A clinical photograph showing a skin lesion. By history, prior skin cancer (patient or family), prior malignancy (patient or family), and no alcohol use. A female patient 75 years old. The patient is Fitzpatrick II — 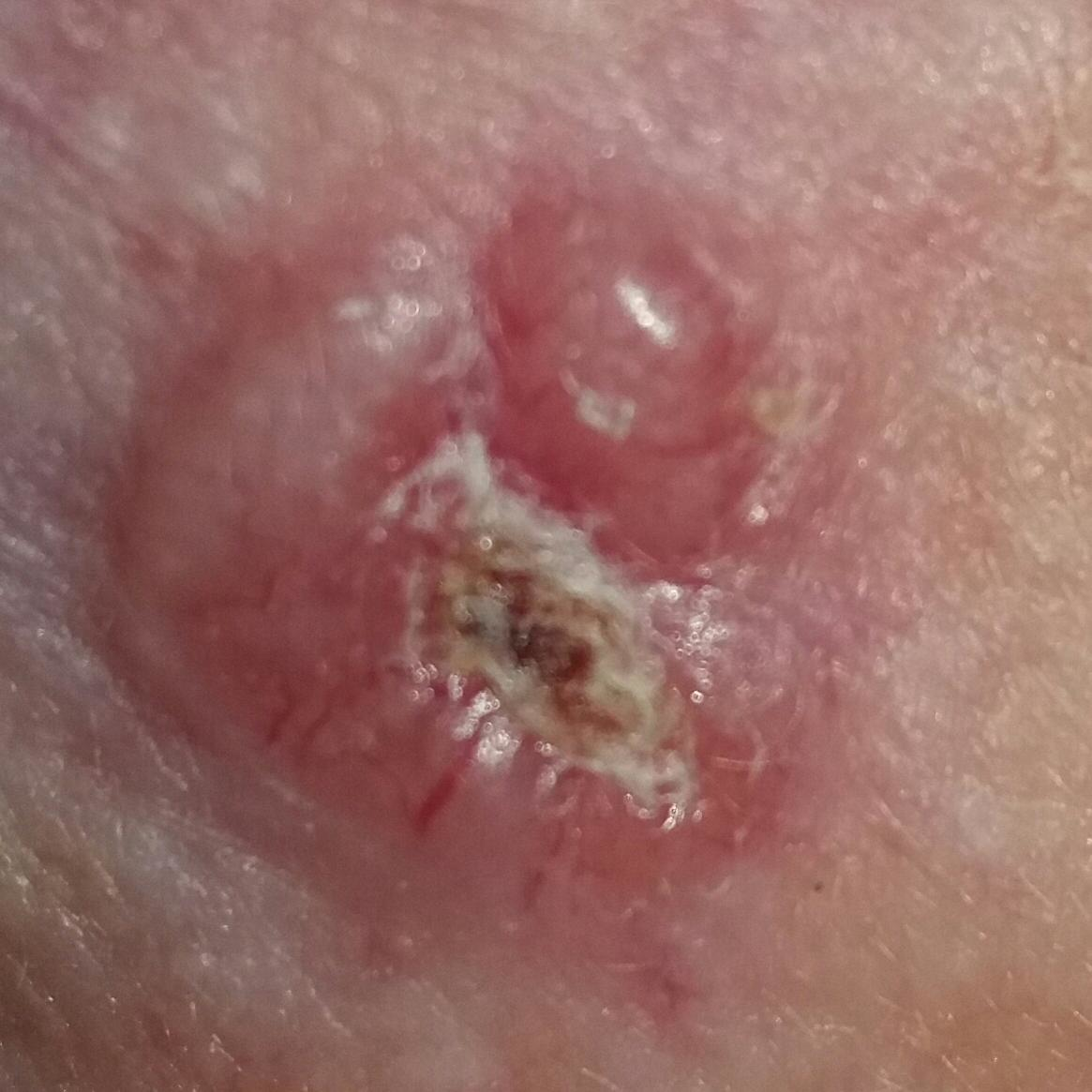The lesion involves the face.
By the patient's account, the lesion itches, is elevated, has bled, and has grown.
Histopathology confirmed a basal cell carcinoma.